The patient is Fitzpatrick phototype II. A clinical photograph showing a skin lesion: 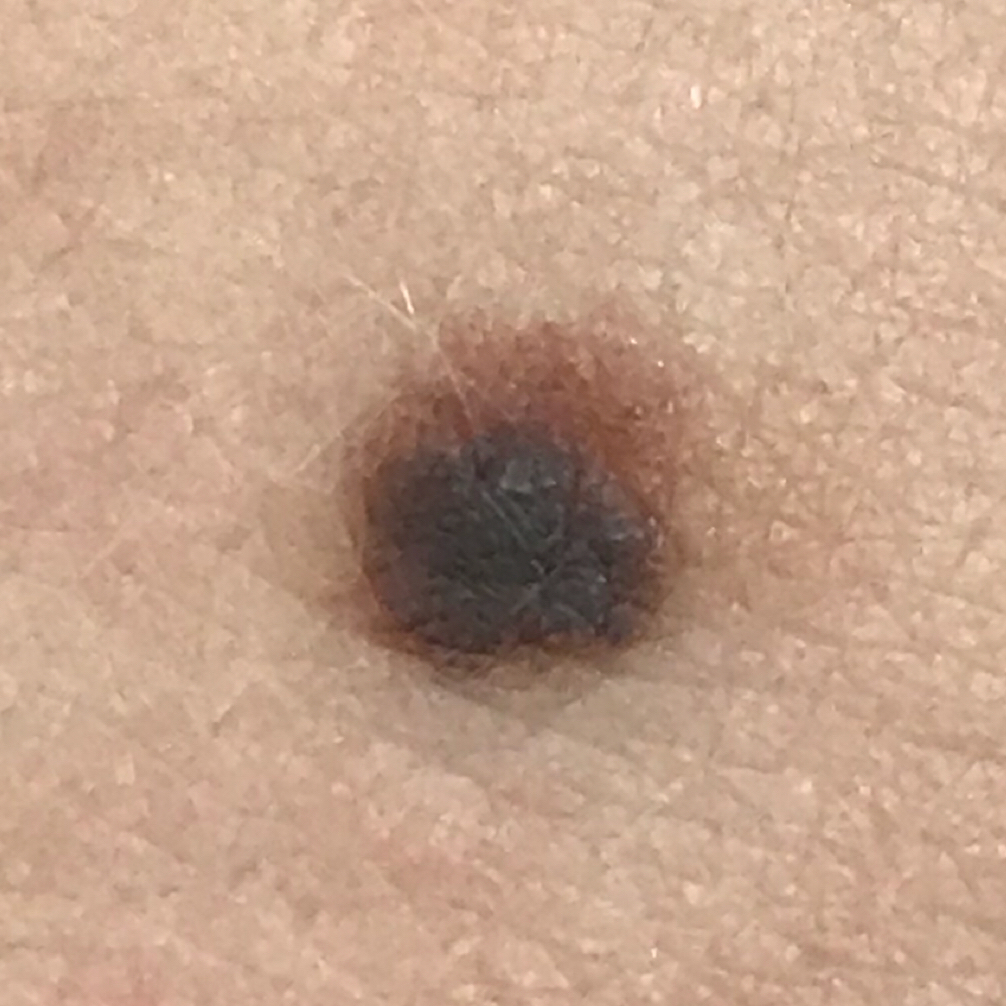| feature | finding |
|---|---|
| body site | the chest |
| lesion size | approx. 5 × 4 mm |
| symptoms | elevation / no bleeding, no itching |
| diagnosis | nevus (biopsy-proven) |